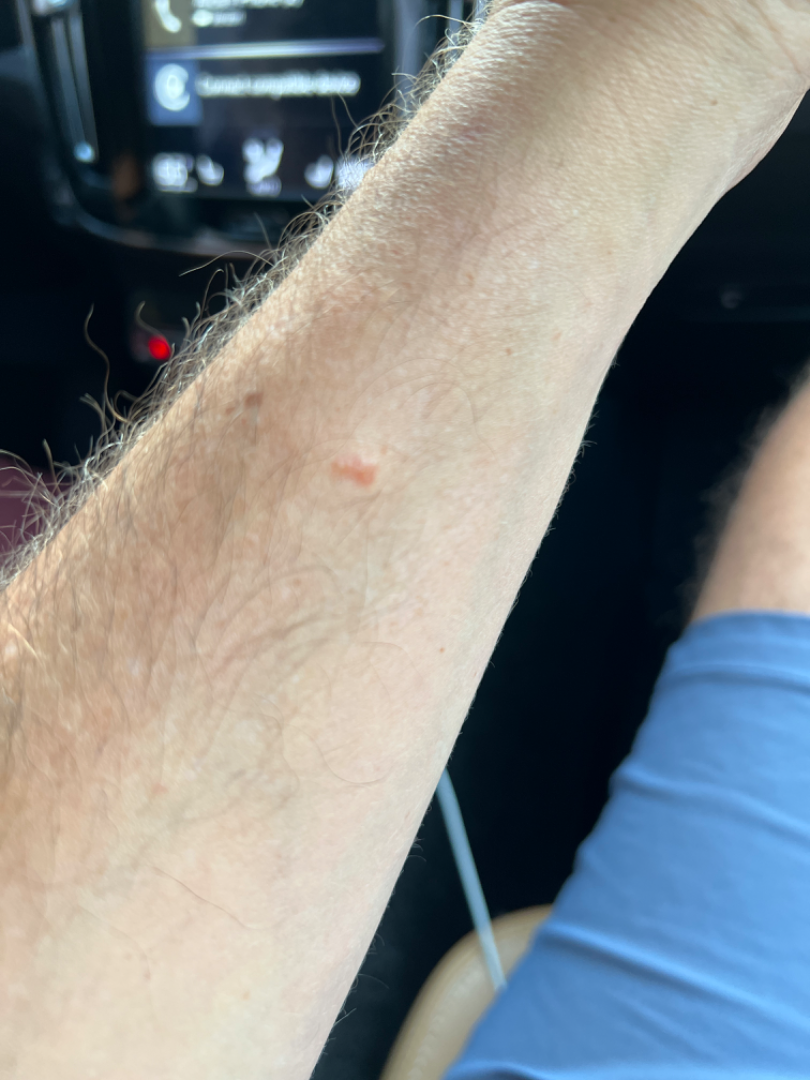Q: Could the case be diagnosed?
A: indeterminate from the photograph